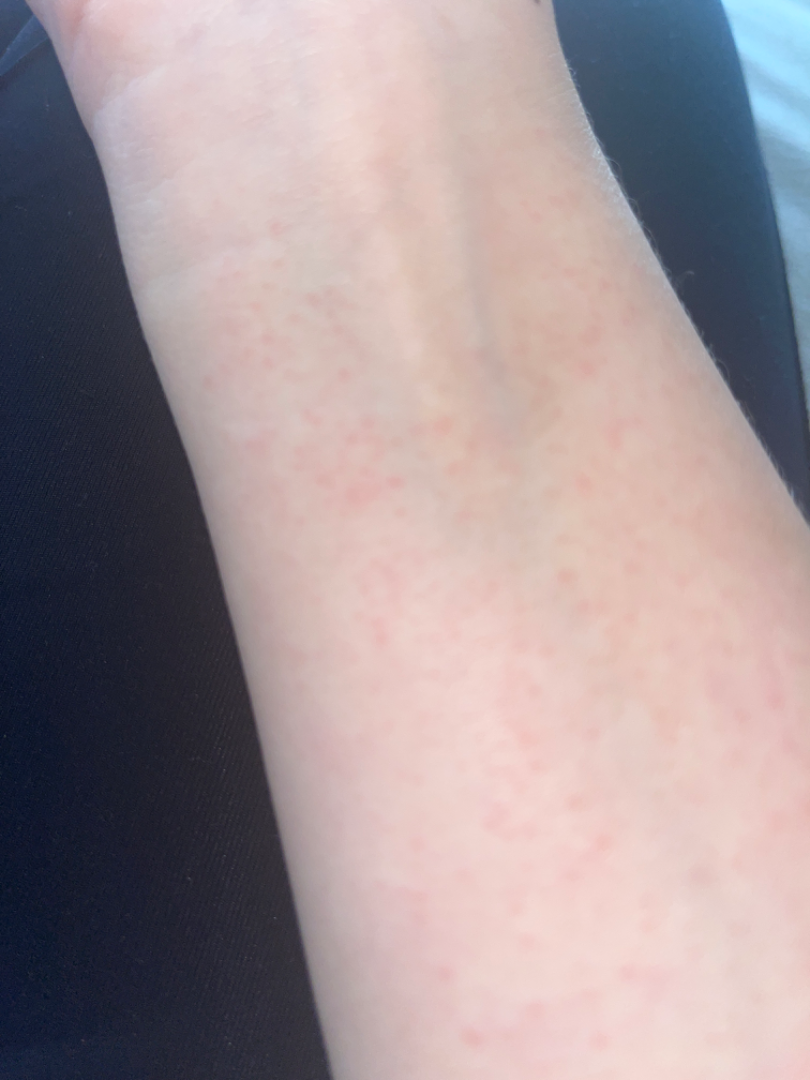Notes:
* assessment · not assessable
* view · close-up